The patient was assessed as Fitzpatrick II · dermoscopy of a skin lesion · a female subject approximately 70 years of age · the chart documents a previous melanoma.
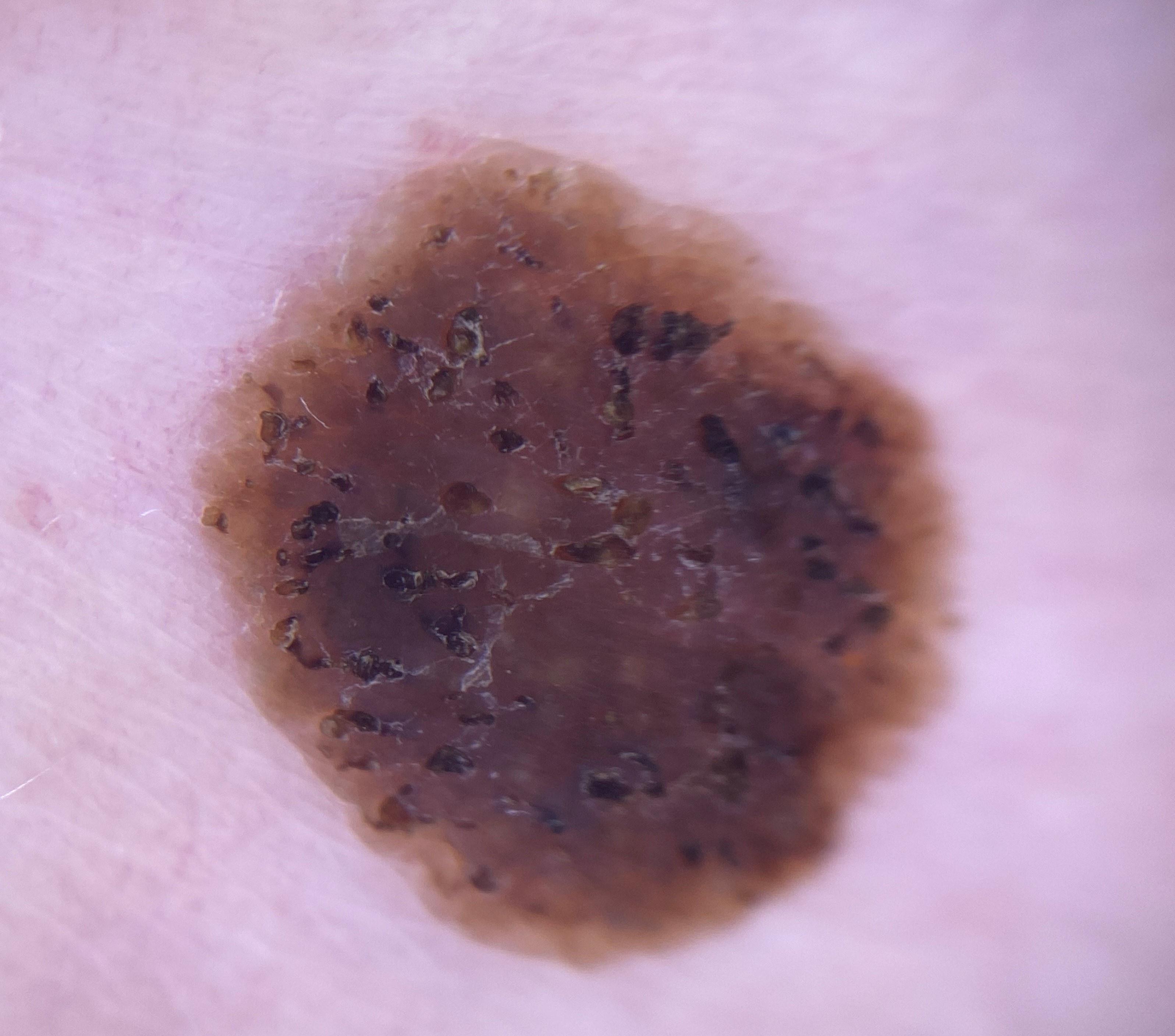The lesion is on the trunk. The diagnostic impression was a seborrheic keratosis.